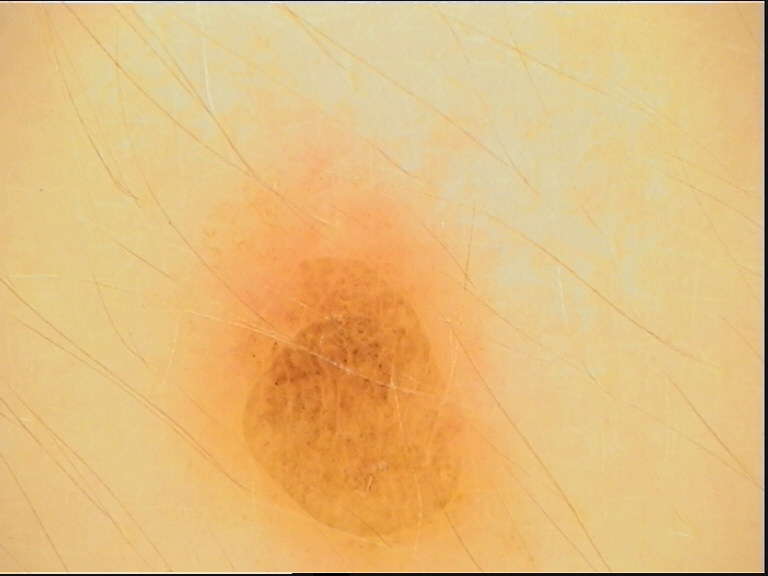modality: dermoscopy, assessment: compound nevus (expert consensus).